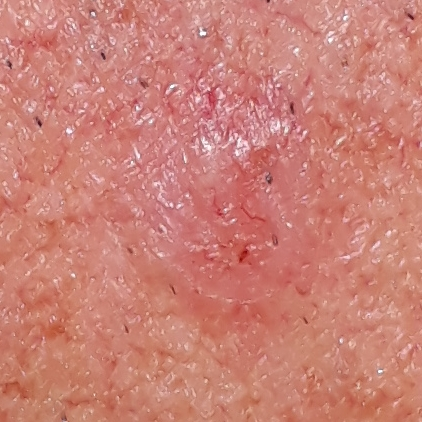Case:
* subject — male, 56 years of age
* image — smartphone clinical photo
* body site — the face
* symptoms — elevation, itching, change in appearance, growth, bleeding
* pathology — basal cell carcinoma (biopsy-proven)